Contact-polarized dermoscopy of a skin lesion. The chart records a prior melanoma. Recorded as skin type II.
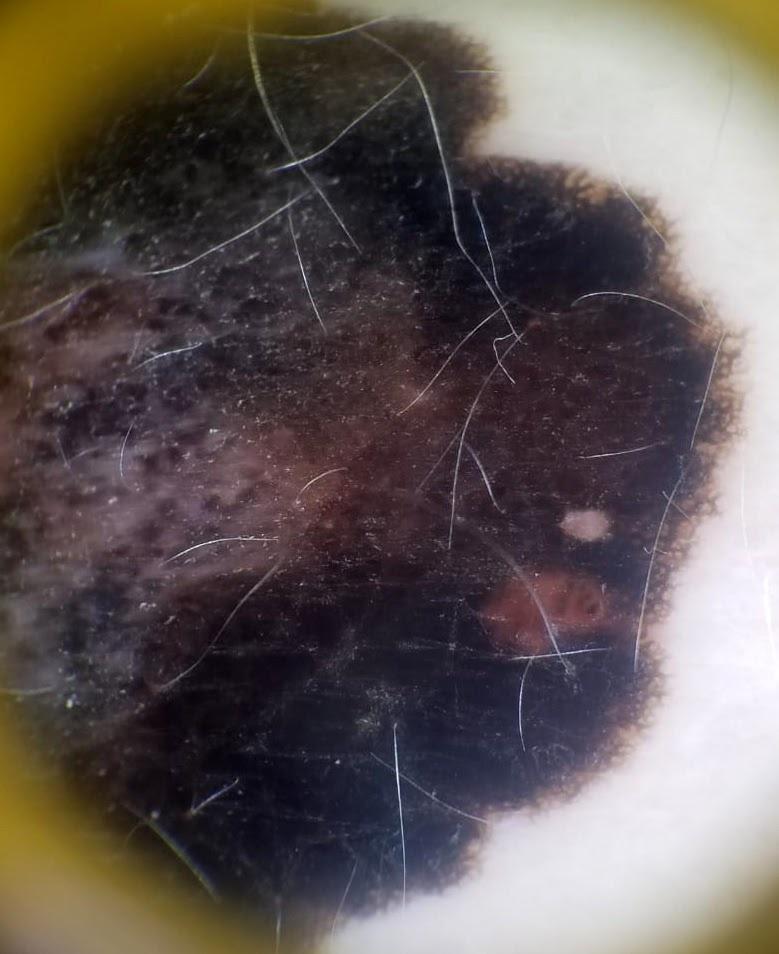The lesion is on the trunk. Biopsy-confirmed as a malignant lesion — a melanoma.